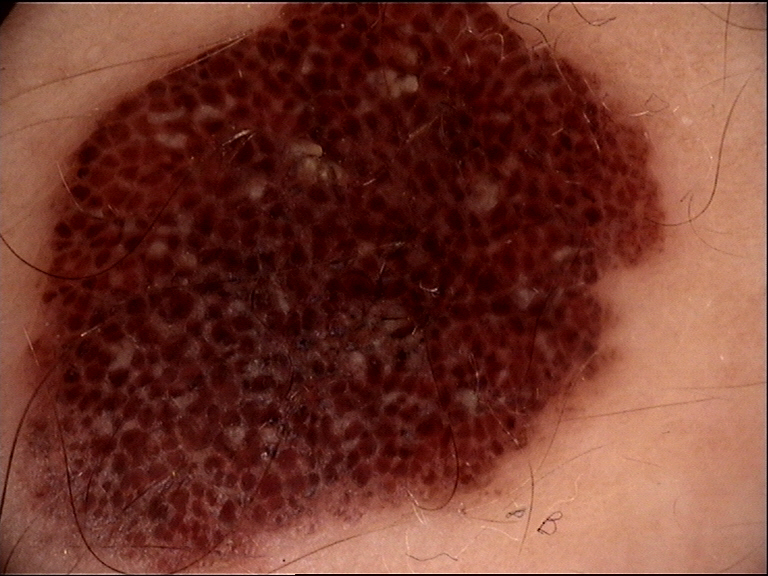Summary: A dermoscopic close-up of a skin lesion. The architecture is that of a banal lesion. Conclusion: Classified as a compound nevus.